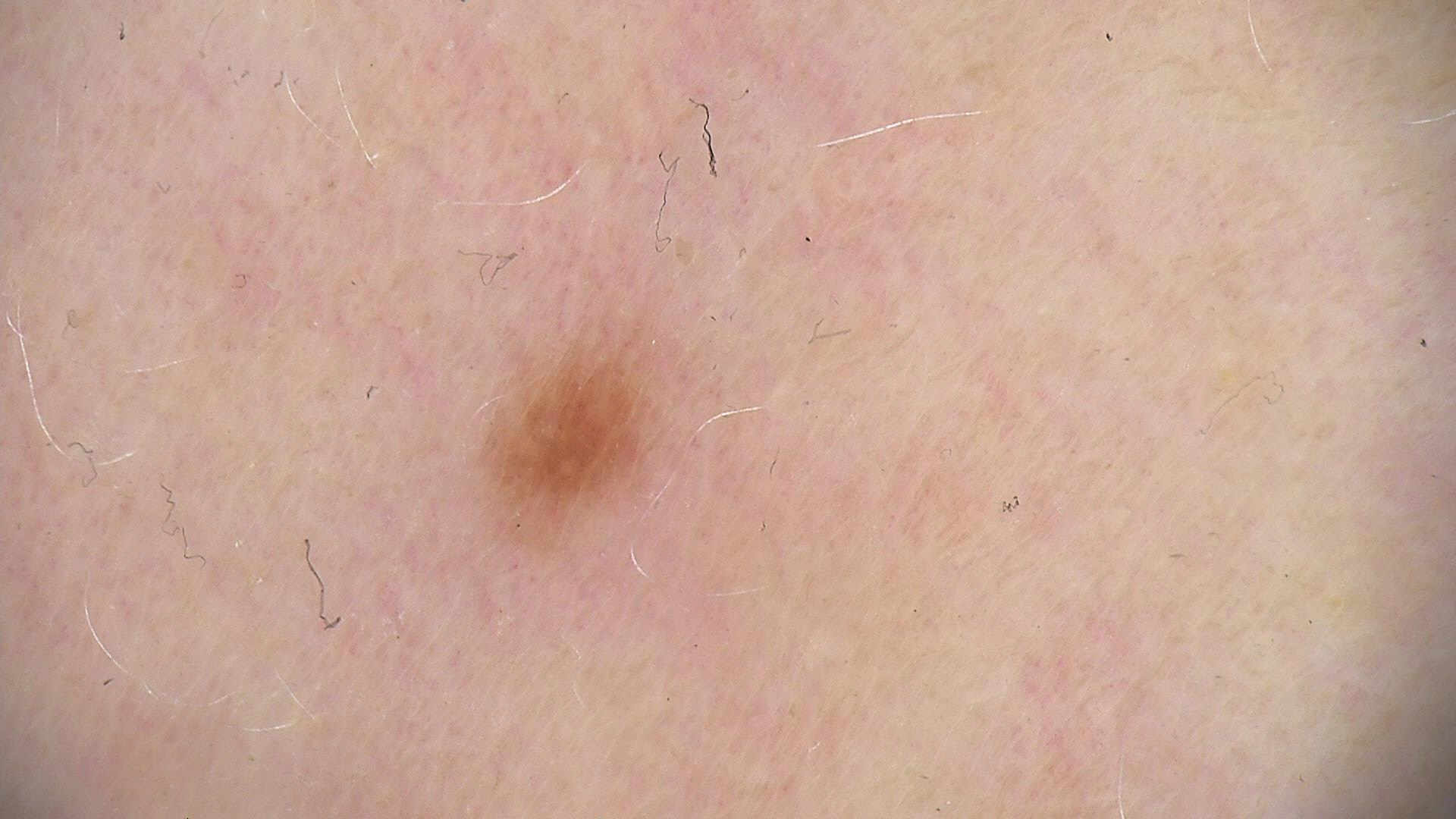Diagnosed as a dysplastic junctional nevus.